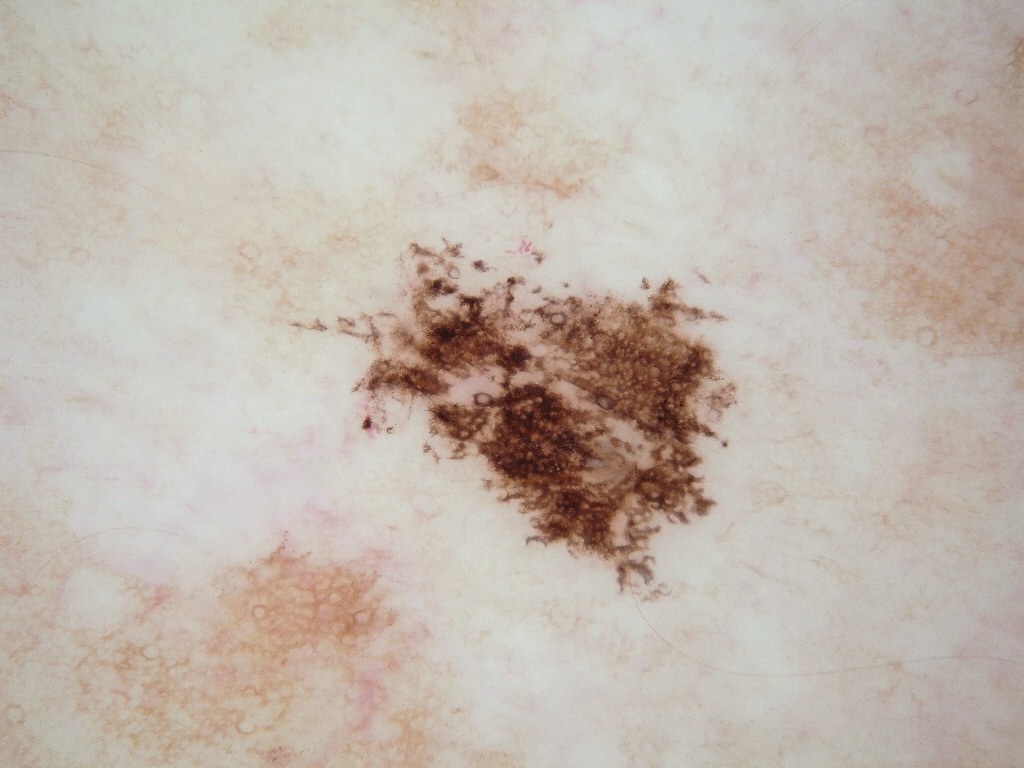• image type · dermoscopy of a skin lesion
• extent · moderate
• absent dermoscopic features · globules and streaks
• location · box(261, 196, 750, 621)
• impression · a benign lesion